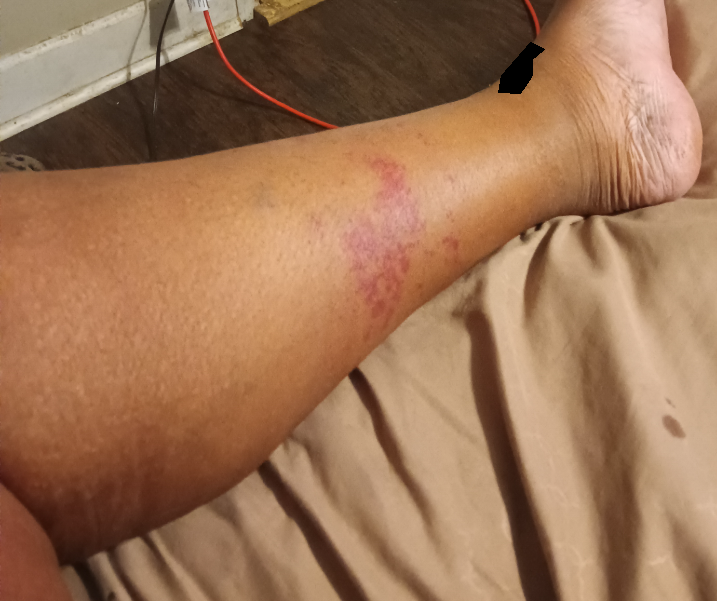image framing = at a distance
dermatologist impression = the differential includes Purpura and Hemangioma, with no clear leading consideration; less probable is Vasculitis of the skin